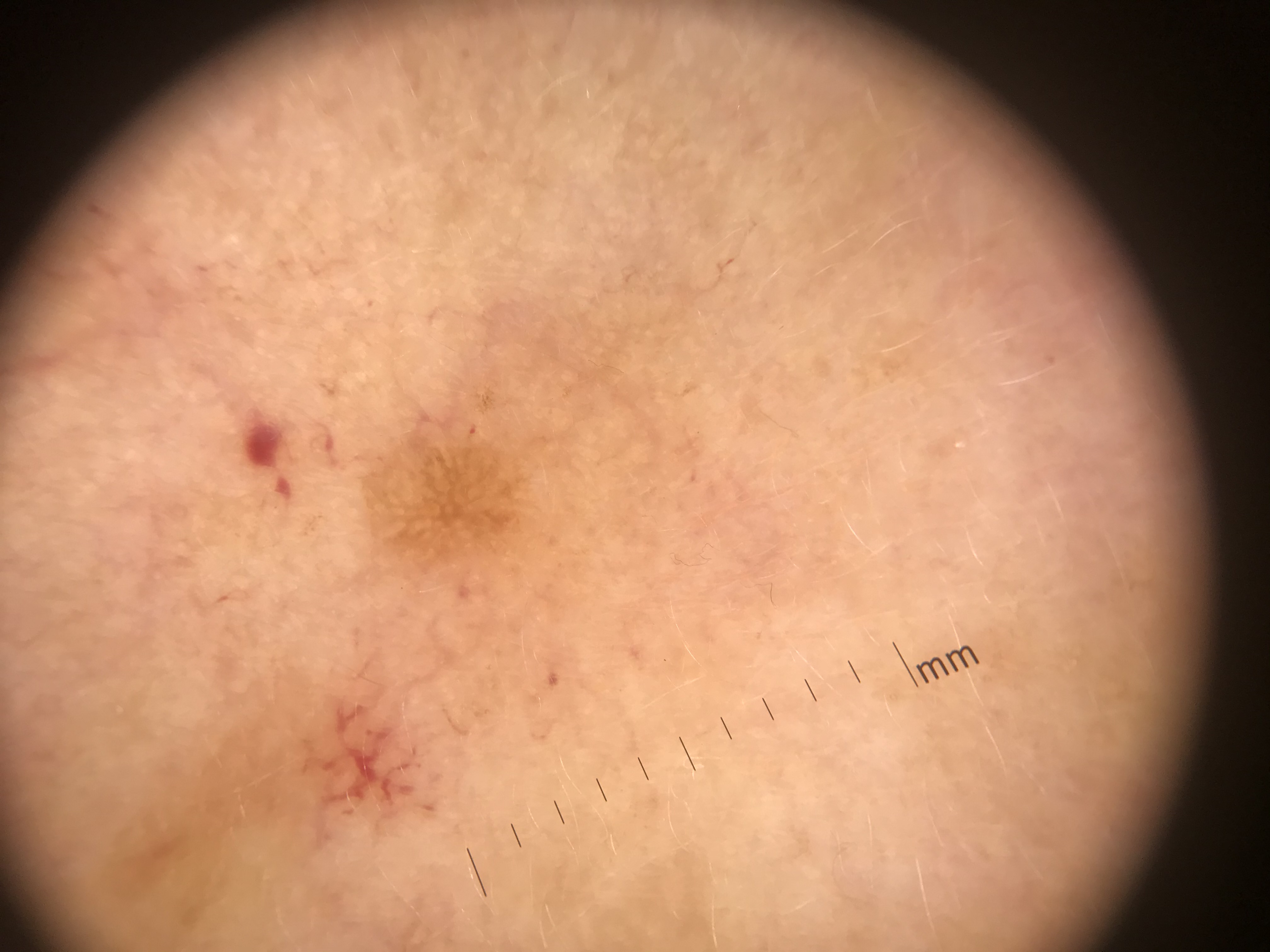| feature | finding |
|---|---|
| imaging | dermatoscopy |
| assessment | seborrheic keratosis (expert consensus) |